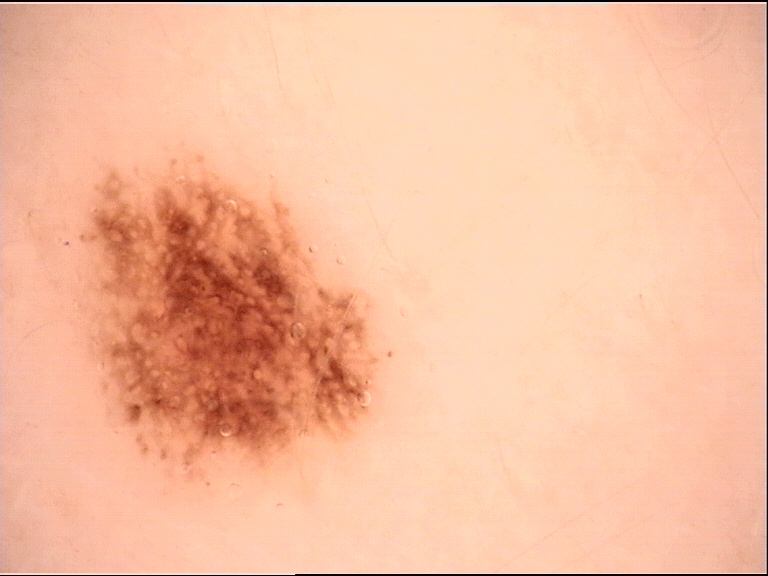Q: What is this lesion?
A: dysplastic junctional nevus (expert consensus)